A dermoscopic close-up of a skin lesion.
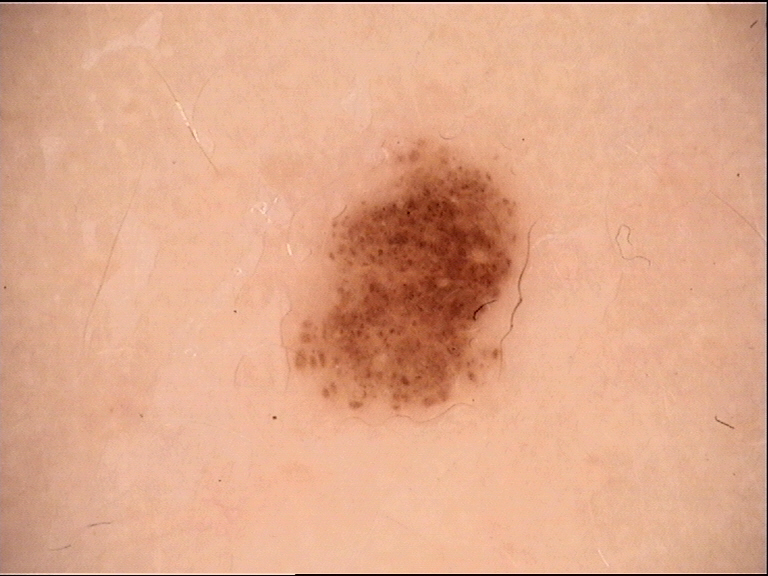Consistent with a dysplastic junctional nevus.